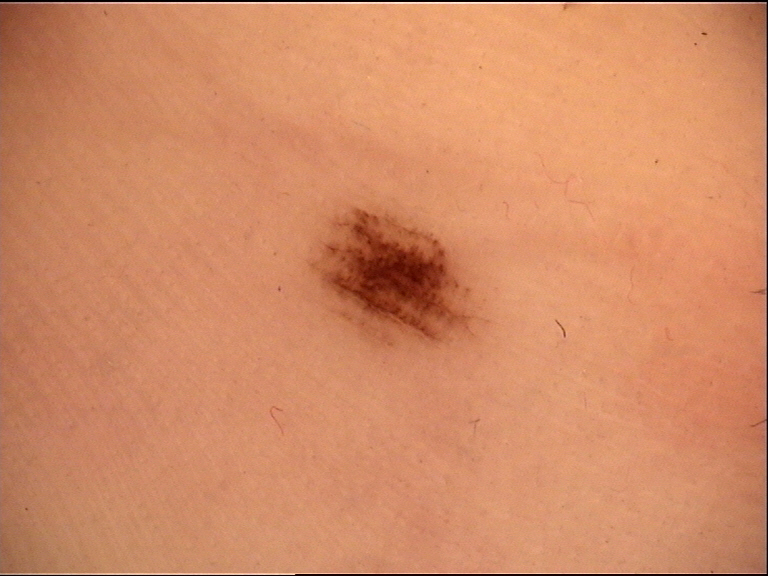A dermoscopic image of a skin lesion.
Diagnosed as a banal lesion — an acral junctional nevus.